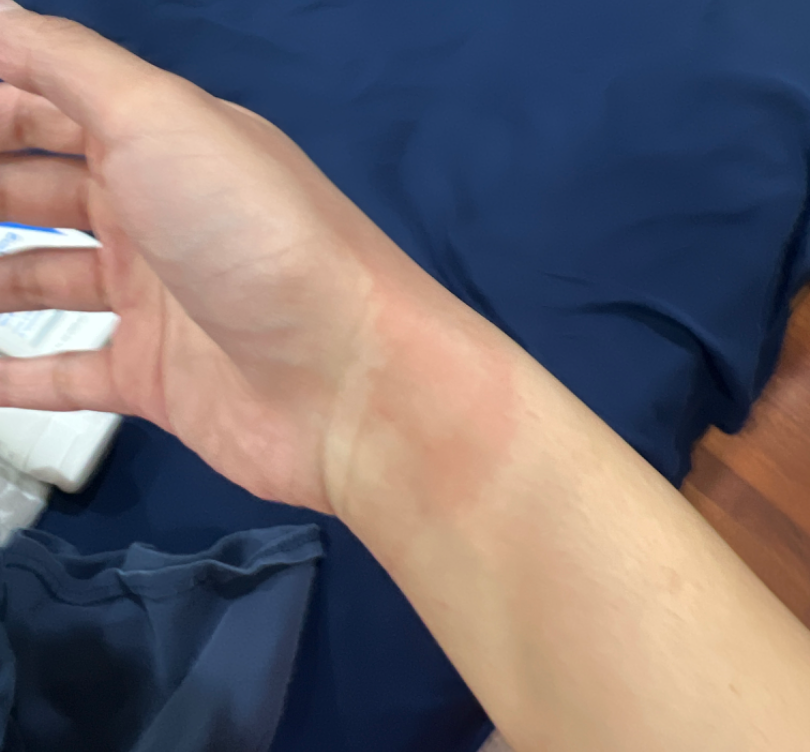photo taken = close-up | skin tone = Fitzpatrick skin type II; lay graders estimated 3 on the MST | impression = favoring Photodermatitis; with consideration of Burn erythema of back of hand.